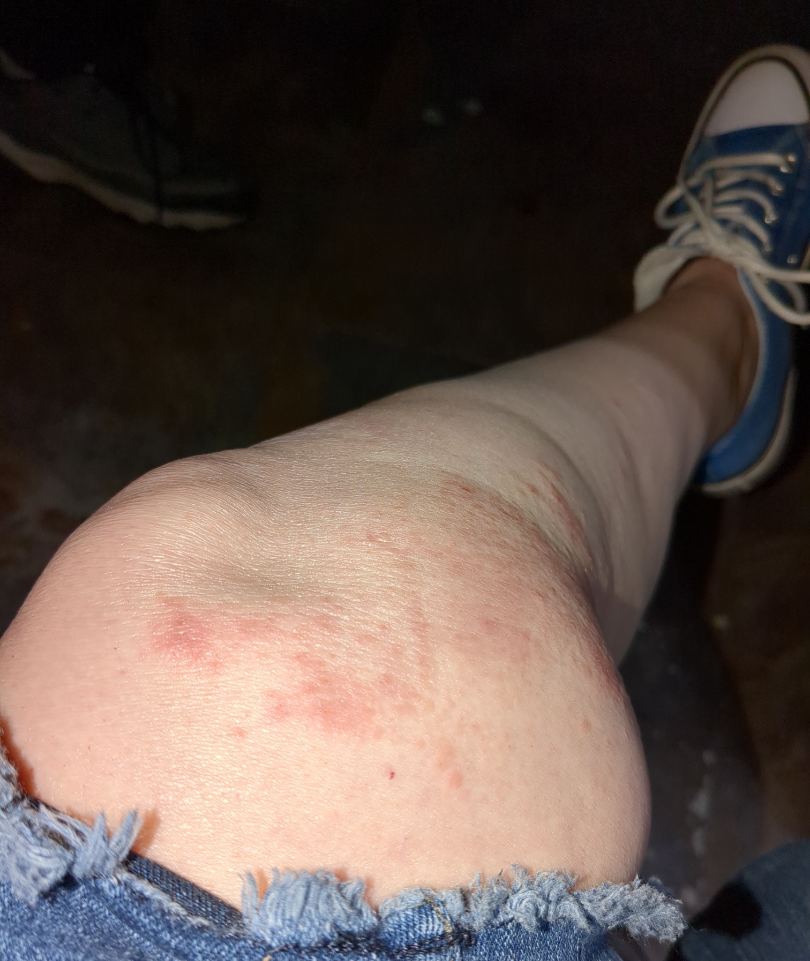The image was not sufficient for the reviewer to characterize the skin condition.